The affected area is the back of the torso, the condition has been present for less than one week, the patient considered this a rash, the contributor notes the lesion is fluid-filled, this is a close-up image, the contributor notes itching and pain:
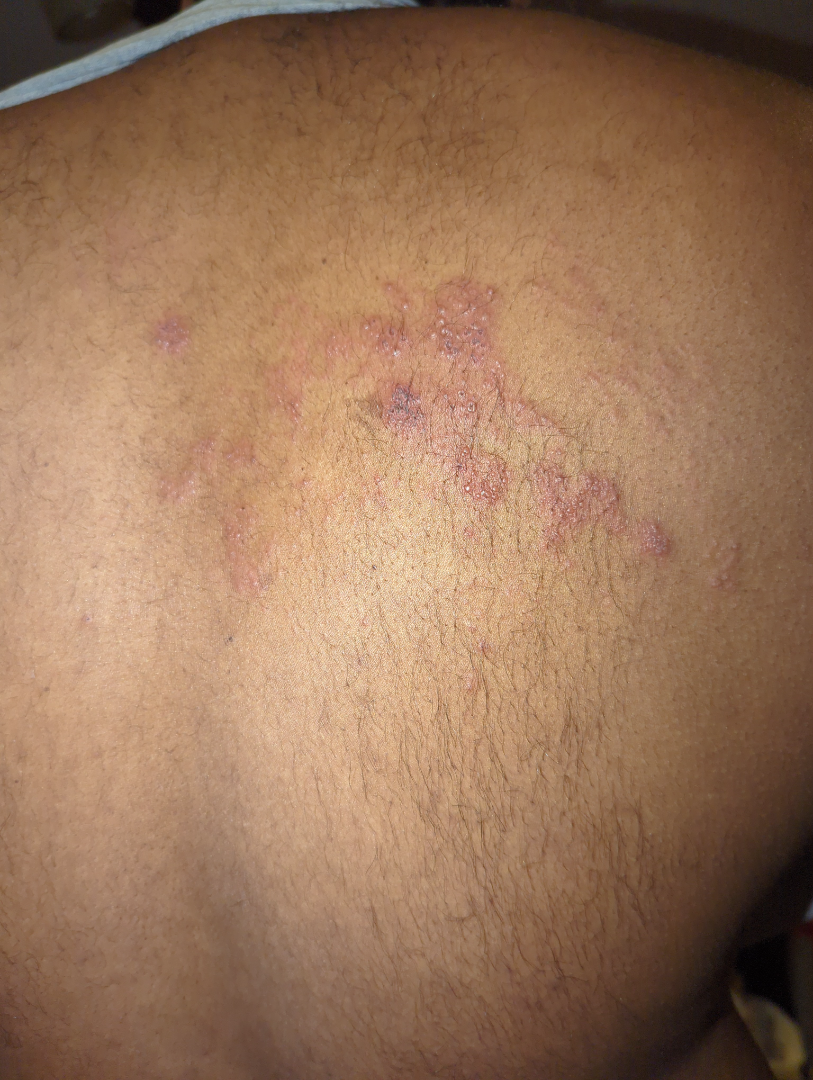On remote review of the image, most consistent with Herpes Zoster.